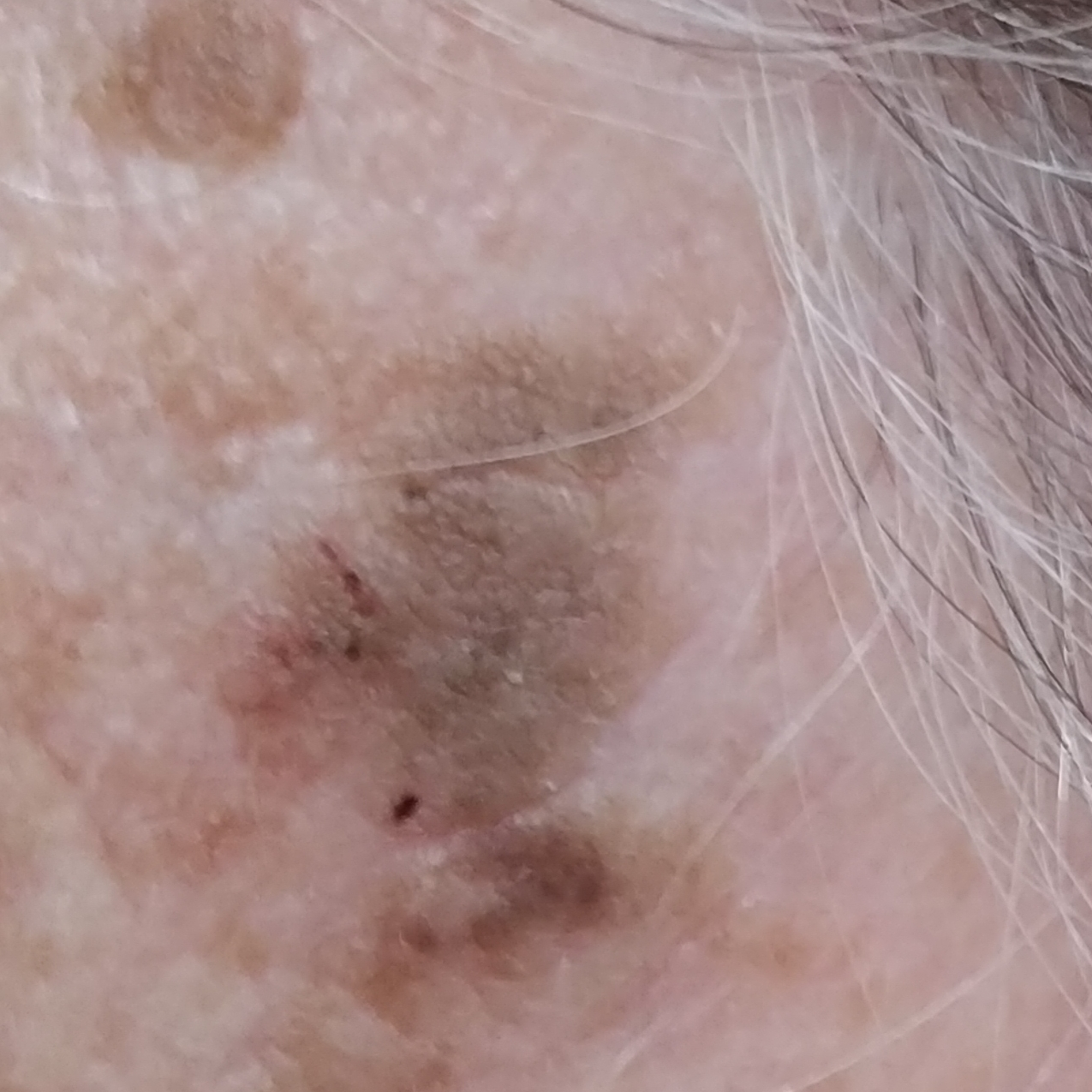A subject in their 70s.
A clinical photo of a skin lesion taken with a smartphone.
The lesion was found on the face.
The patient describes that the lesion is elevated.
Consistent with a seborrheic keratosis.